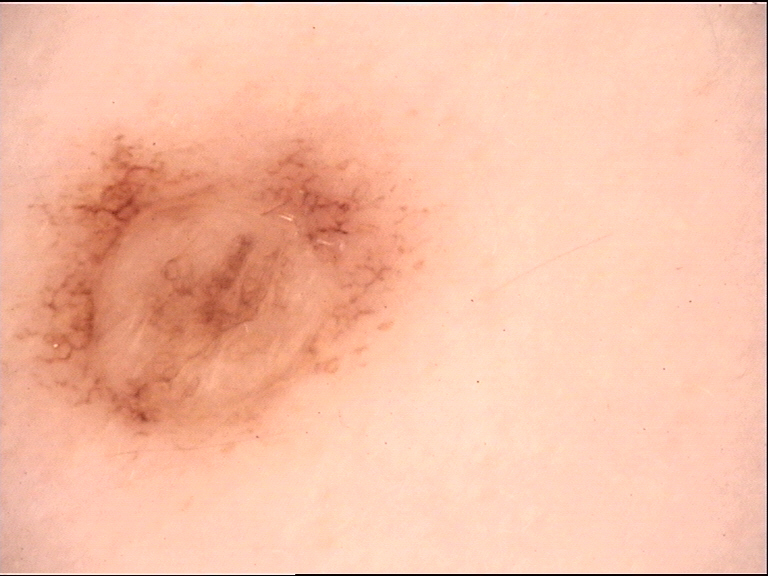Impression: Consistent with a dermal nevus.